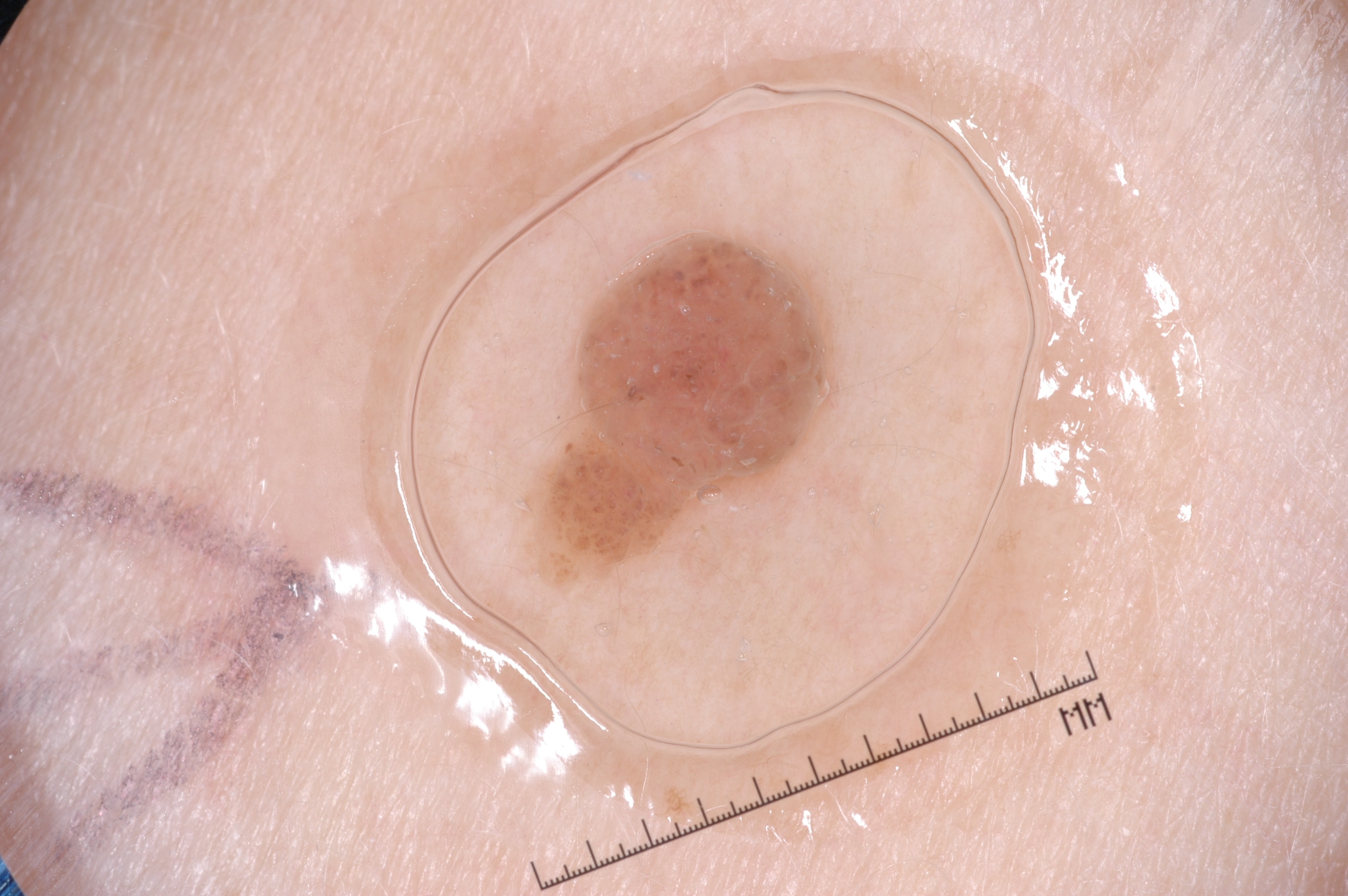A dermoscopic view of a skin lesion.
The patient is a female aged approximately 40.
In (x1, y1, x2, y2) order, lesion location: box(537, 231, 832, 567).
The lesion covers approximately 6% of the dermoscopic field.
Dermoscopically, the lesion shows no milia-like cysts, pigment network, streaks, or negative network.
Clinically diagnosed as a melanocytic nevus, a benign skin lesion.